A dermoscopic close-up of a skin lesion; a male patient, aged around 55: 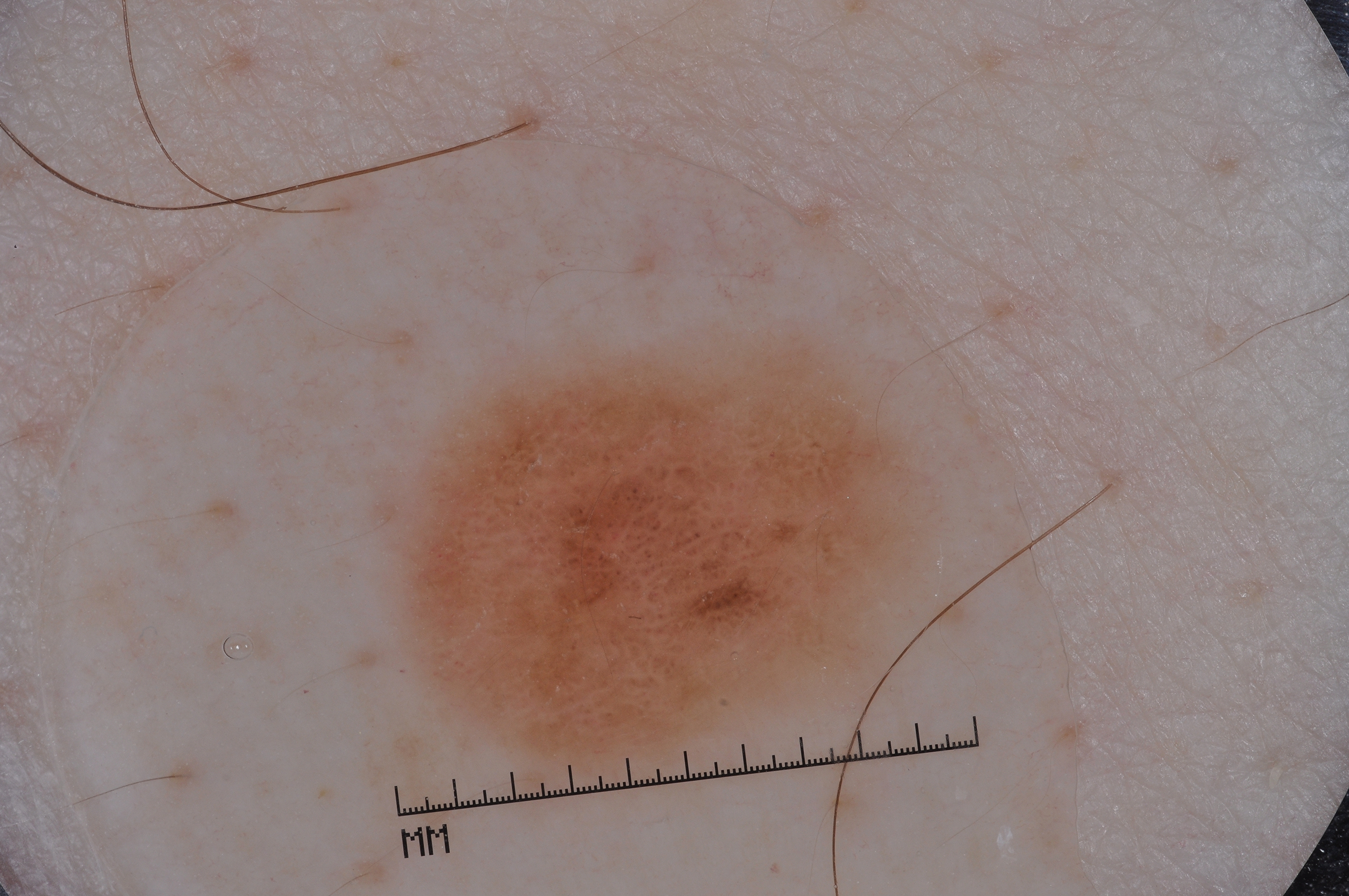A mid-sized lesion within the field.
As (left, top, right, bottom), the lesion is located at [379,337,927,791].
On dermoscopy, the lesion shows negative network.
Histopathological examination showed a melanoma, a malignant skin lesion.